Dermoscopy of a skin lesion.
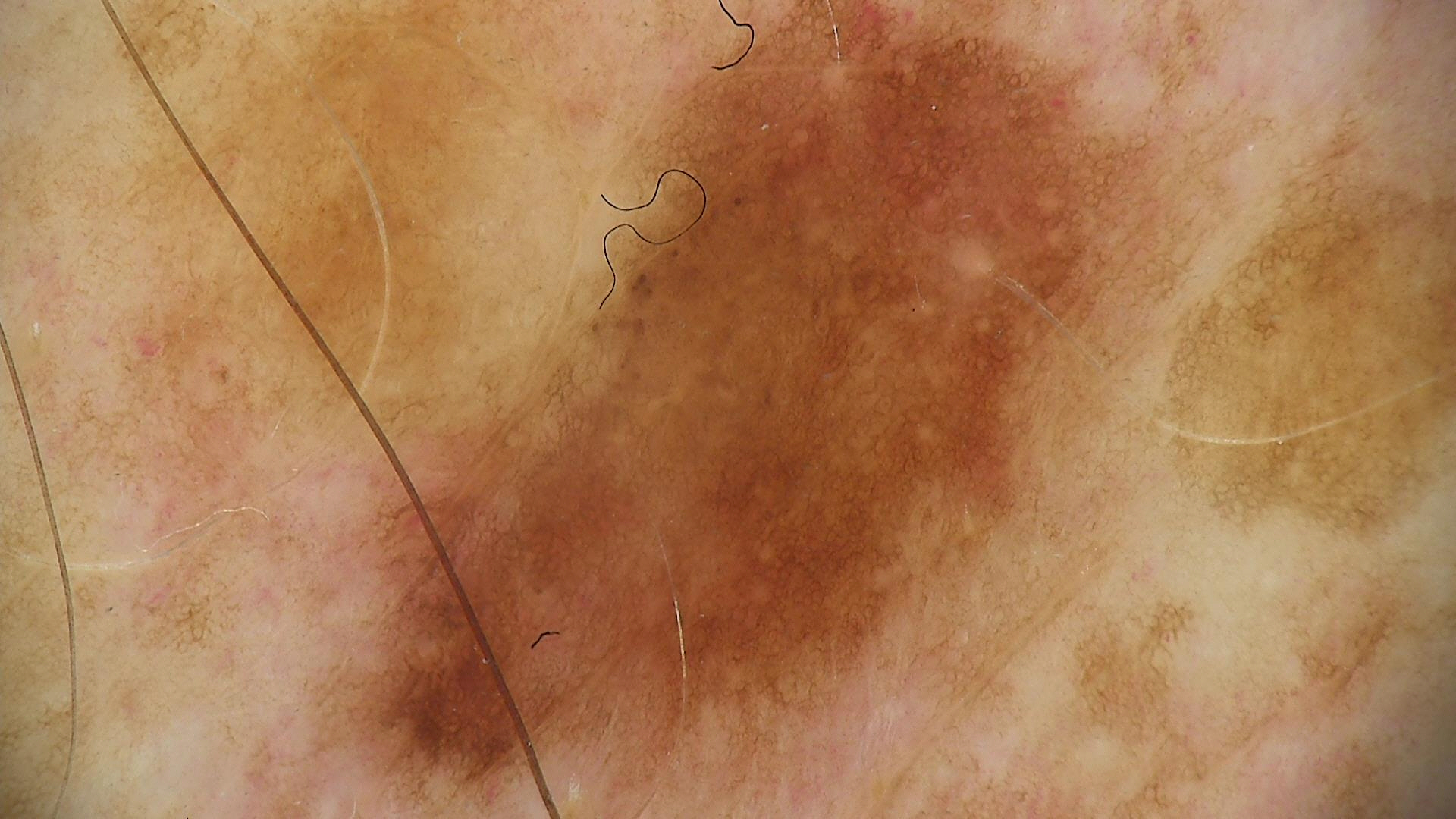Diagnosed as a benign lesion — a dysplastic junctional nevus.